A dermatoscopic image of a skin lesion: 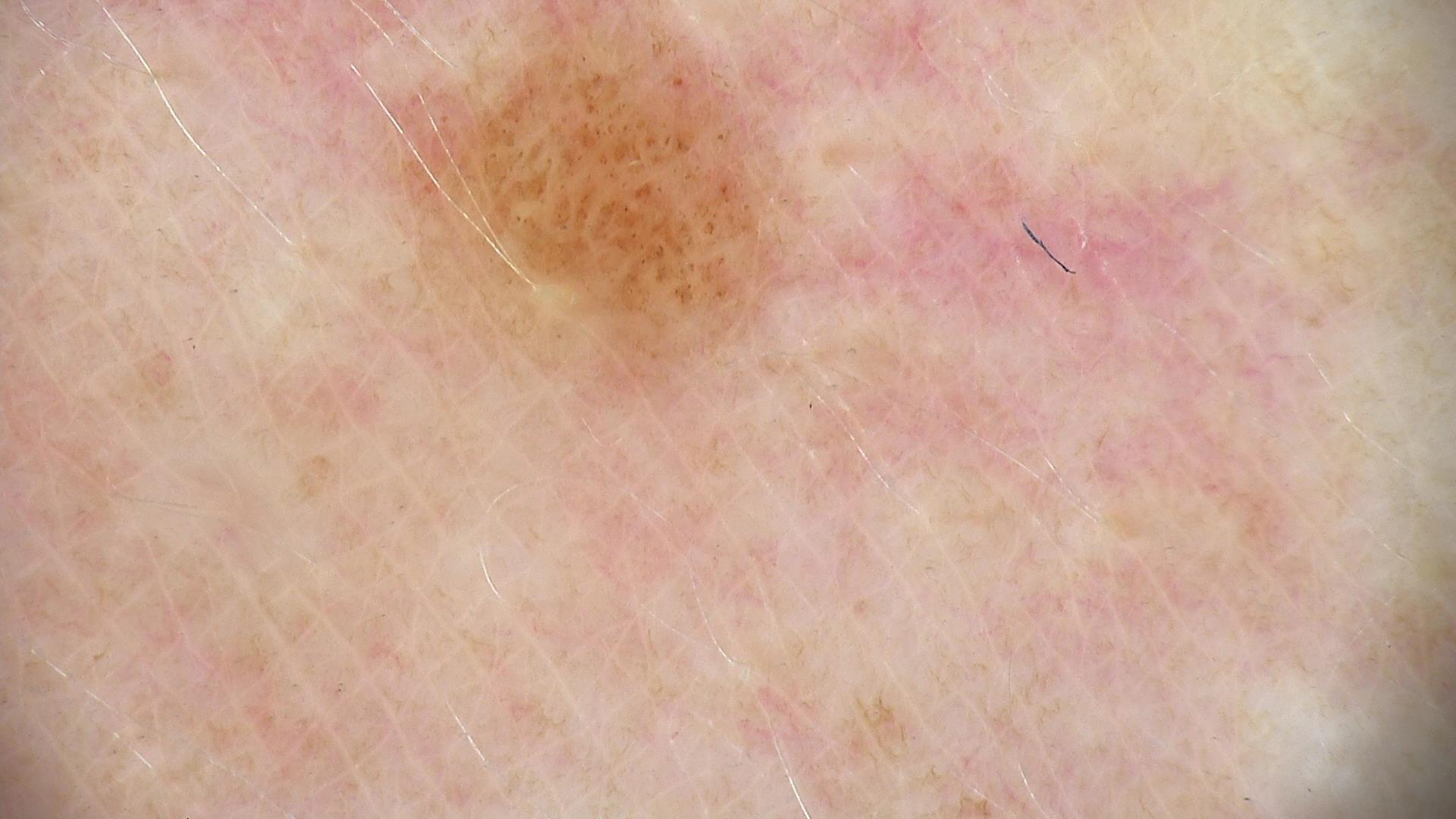diagnosis: junctional nevus (expert consensus).